A dermoscopic image of a skin lesion: 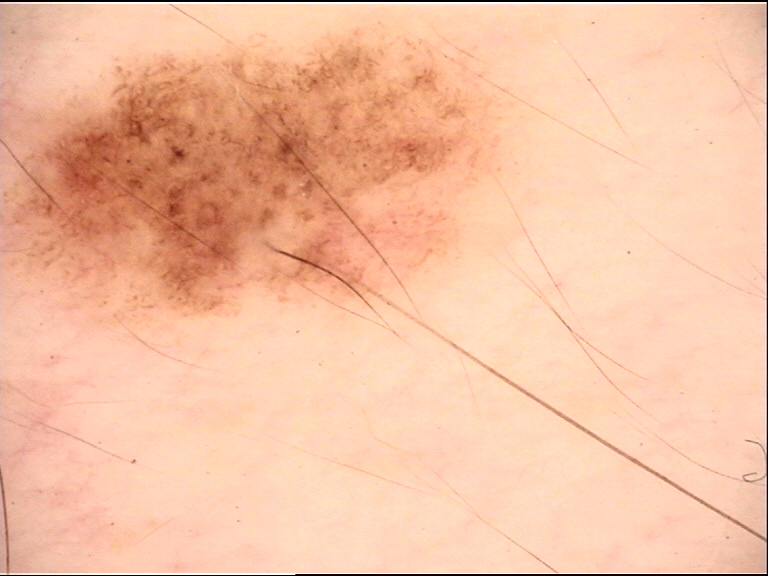Conclusion:
The diagnostic label was a benign lesion — a dysplastic junctional nevus.